A contact-polarized dermoscopy image of a skin lesion · per the chart, a previous melanoma but no first-degree relative with melanoma · recorded as Fitzpatrick skin type II · a male subject roughly 50 years of age.
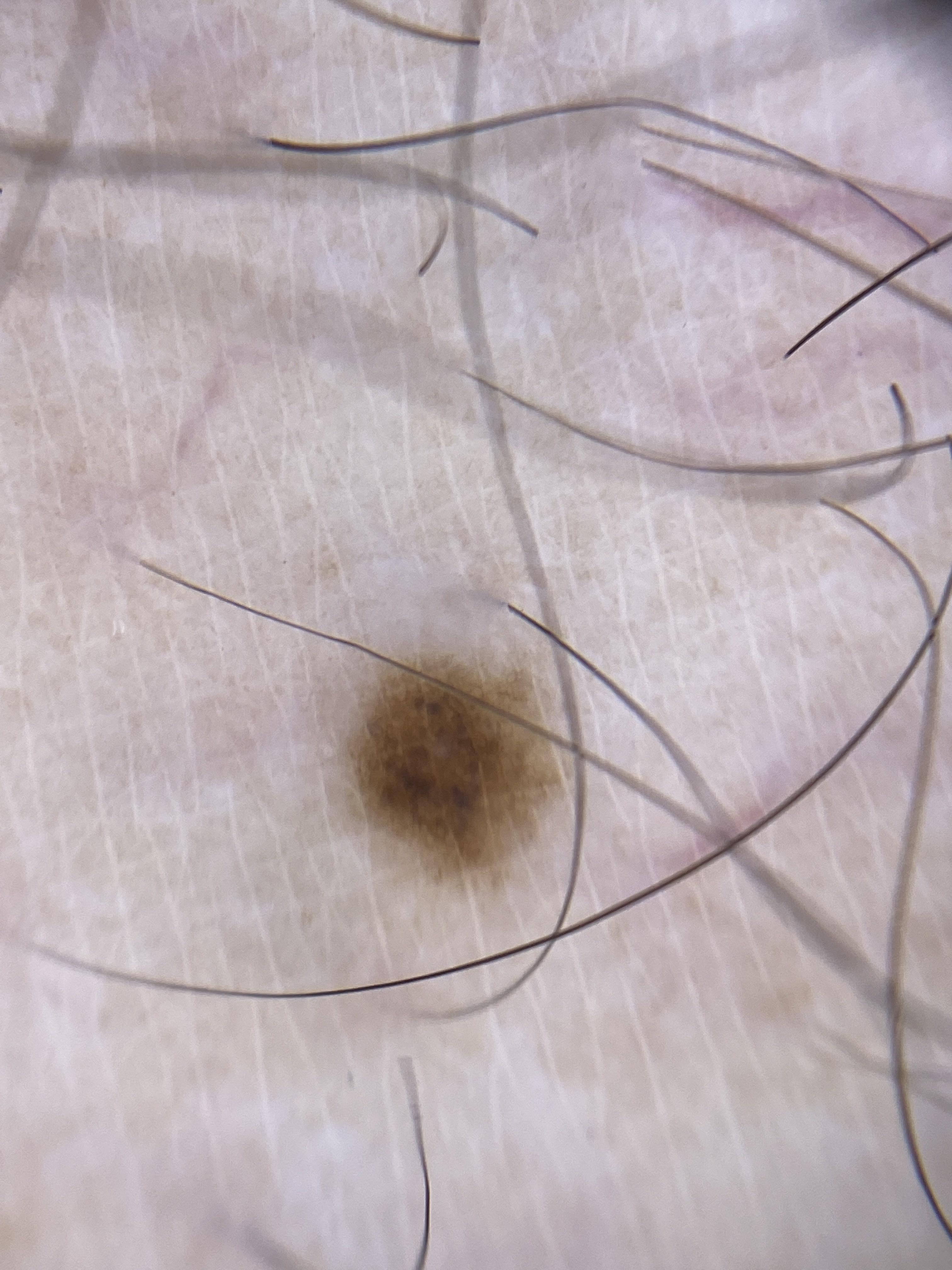The lesion involves an upper extremity. The diagnostic impression was a benign lesion — a nevus.